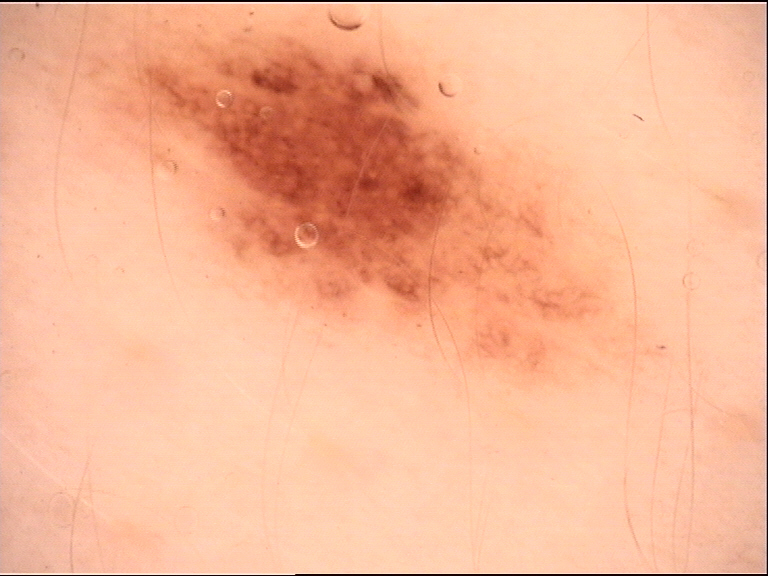Case:
A dermatoscopic image of a skin lesion.
Conclusion:
Labeled as a benign lesion — a dysplastic junctional nevus.